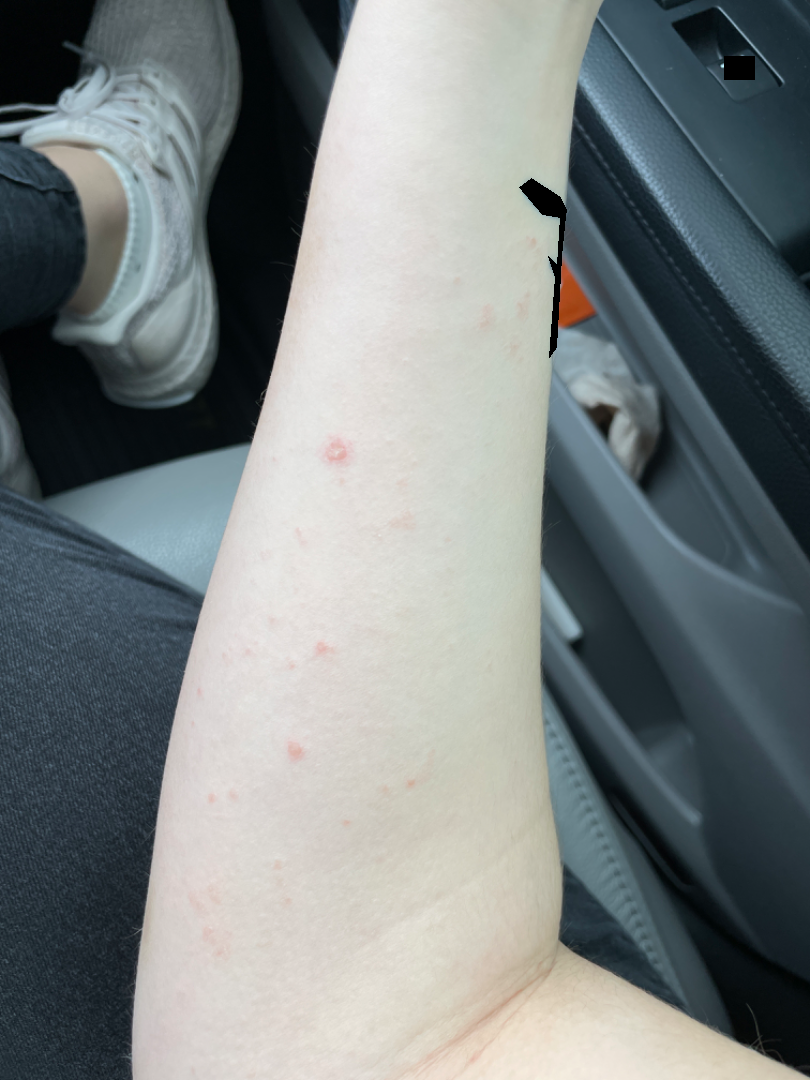| key | value |
|---|---|
| assessment | could not be assessed |